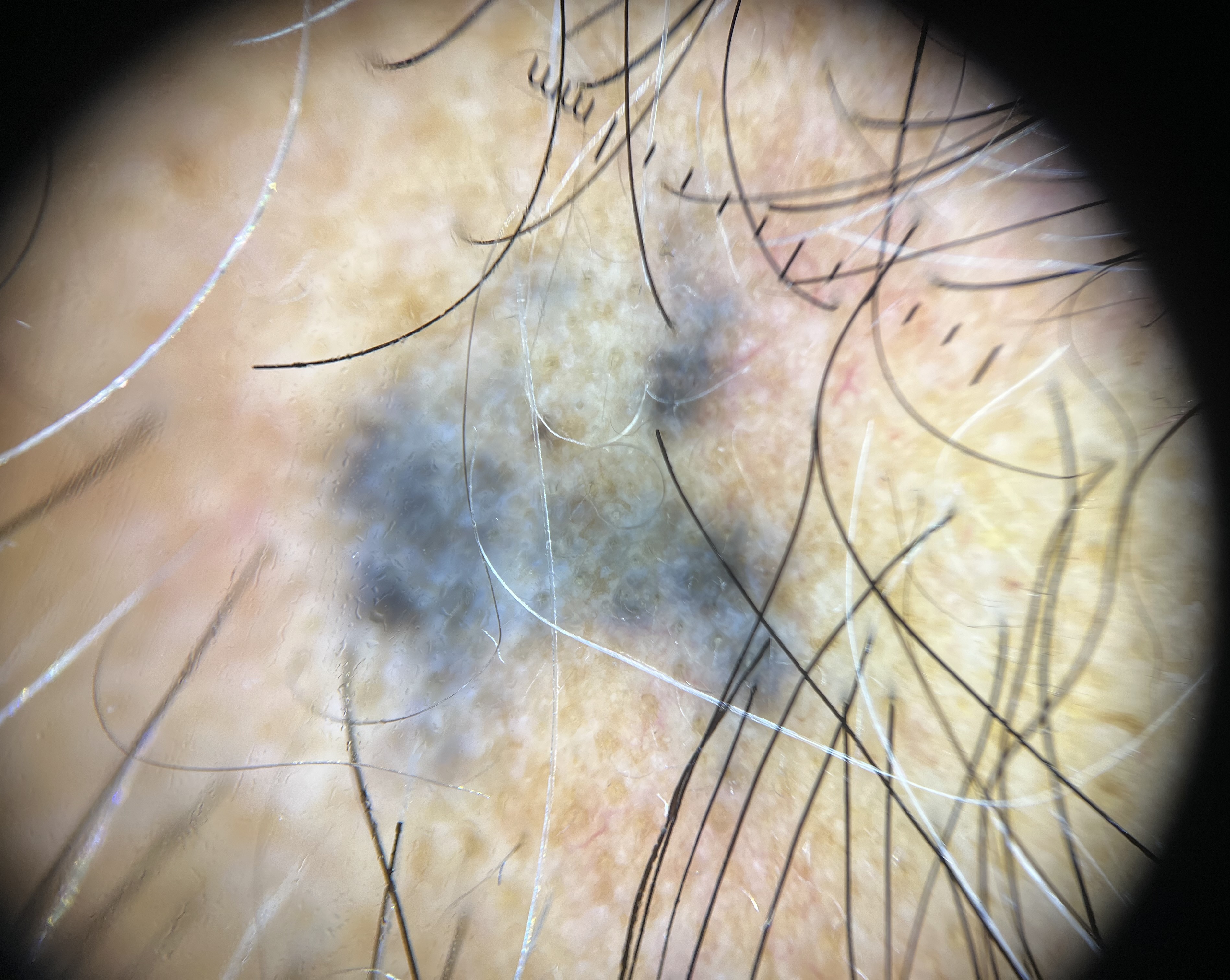Findings:
- modality — dermoscopy
- class — blue nevus (expert consensus)